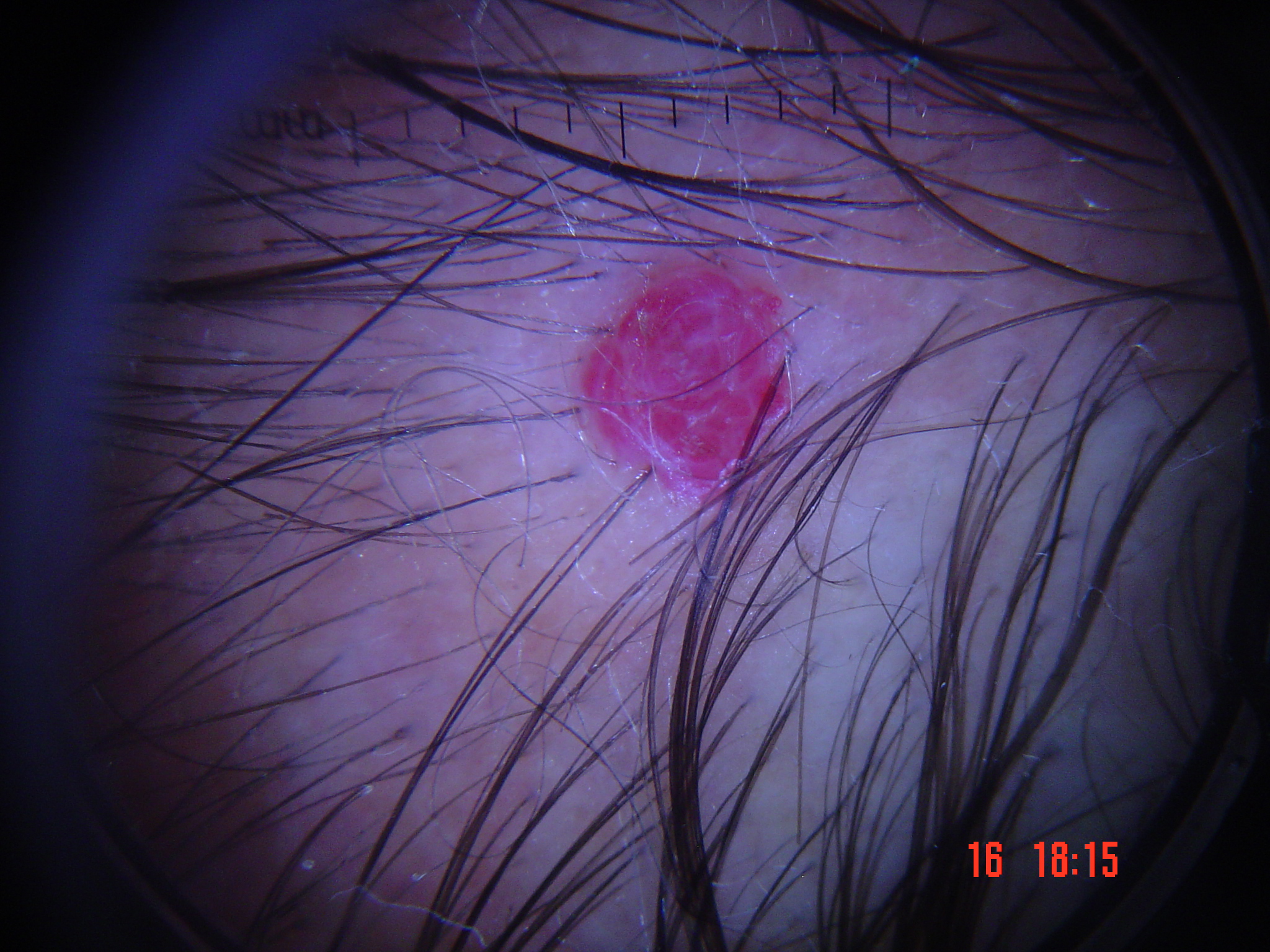Case:
Dermoscopy of a skin lesion. The morphology is that of a vascular lesion.
Conclusion:
The diagnostic label was a benign lesion — a hemangioma.